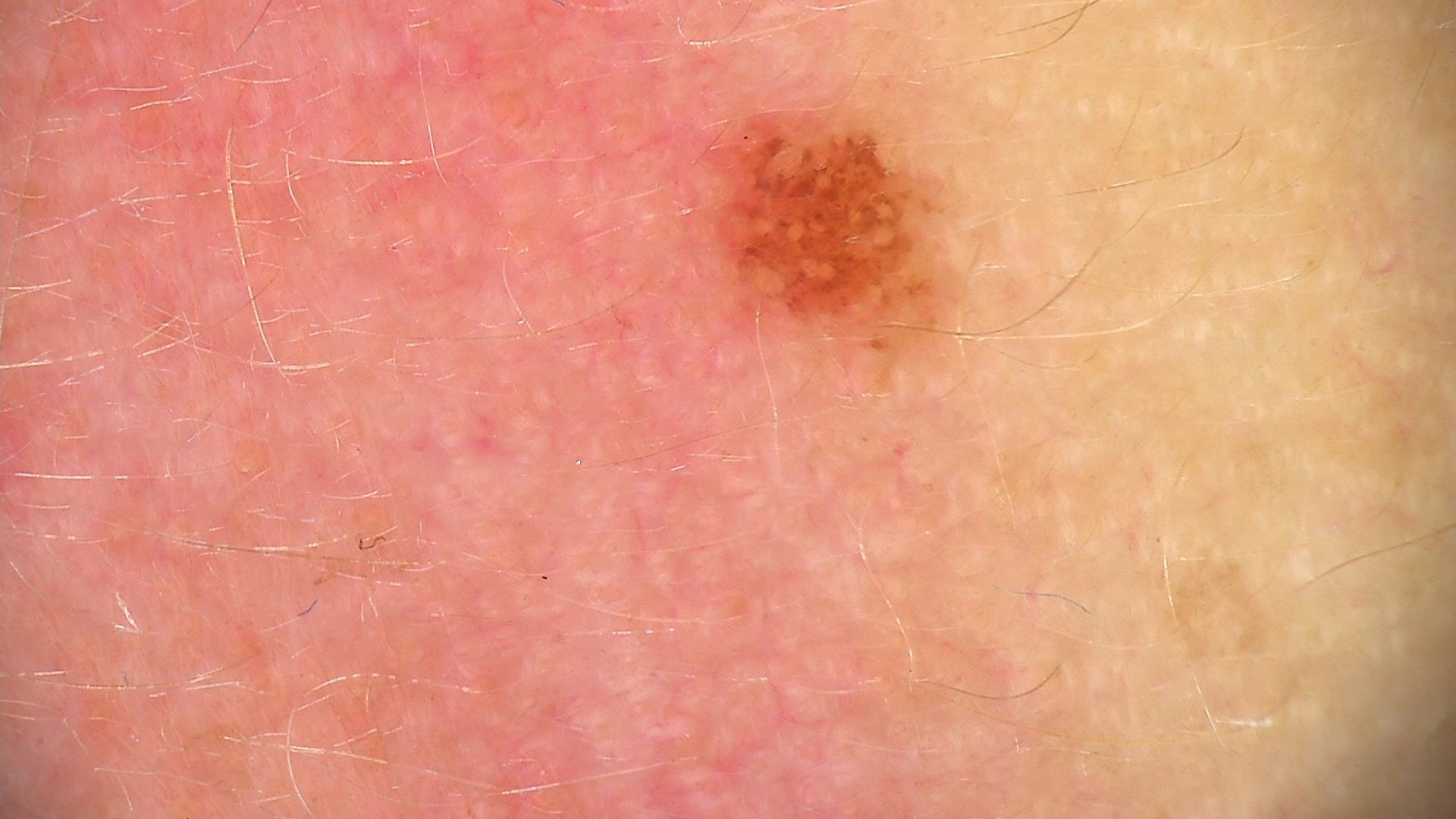A skin lesion imaged with a dermatoscope.
This is a compound, banal lesion.
Labeled as a Miescher nevus.